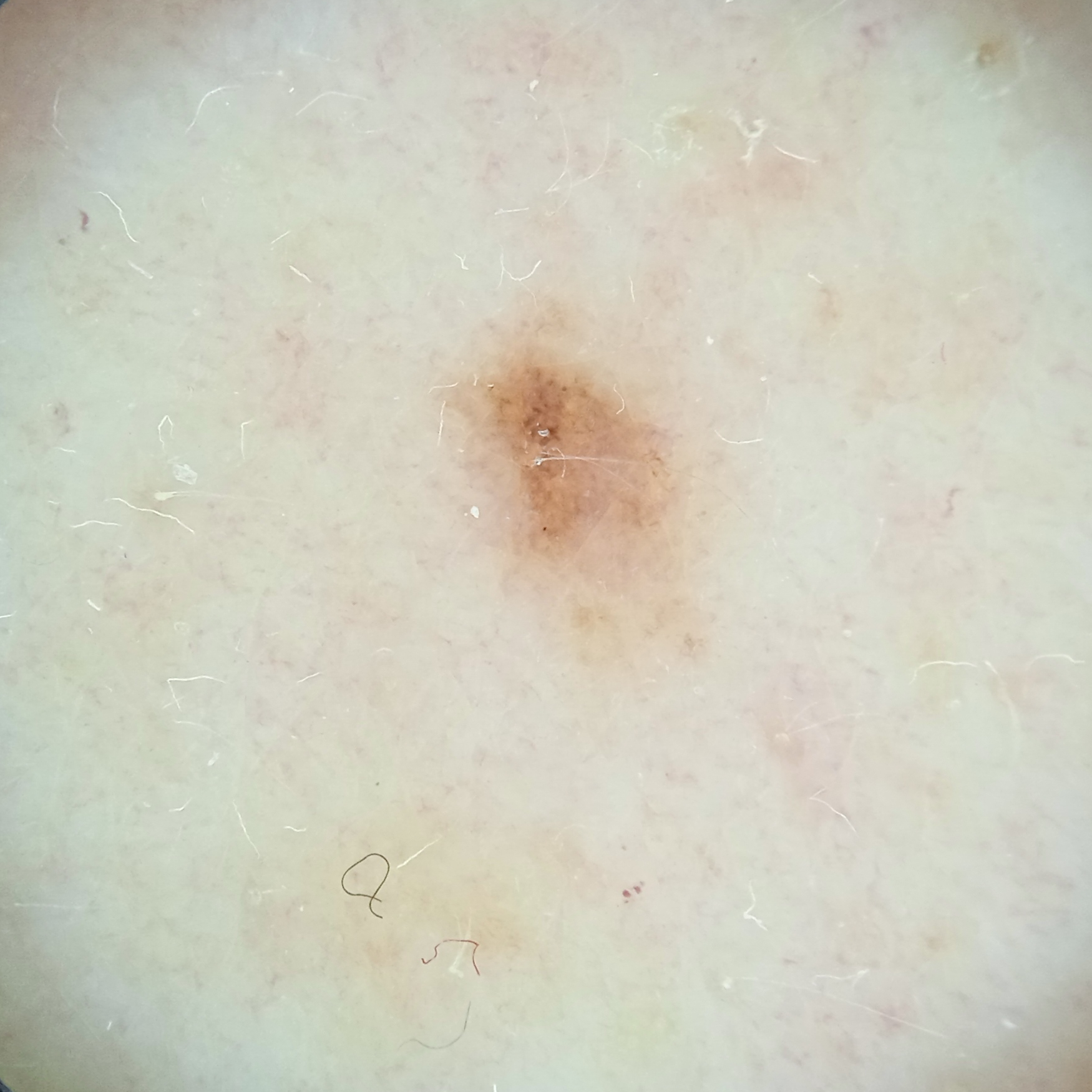By self-report, immunosuppression, a prior organ transplant, no personal history of skin cancer, and no family history of skin cancer. A female patient age 55. The lesion is located on the back. The lesion is about 2.5 mm across. The consensus diagnosis for this lesion was a melanocytic nevus.